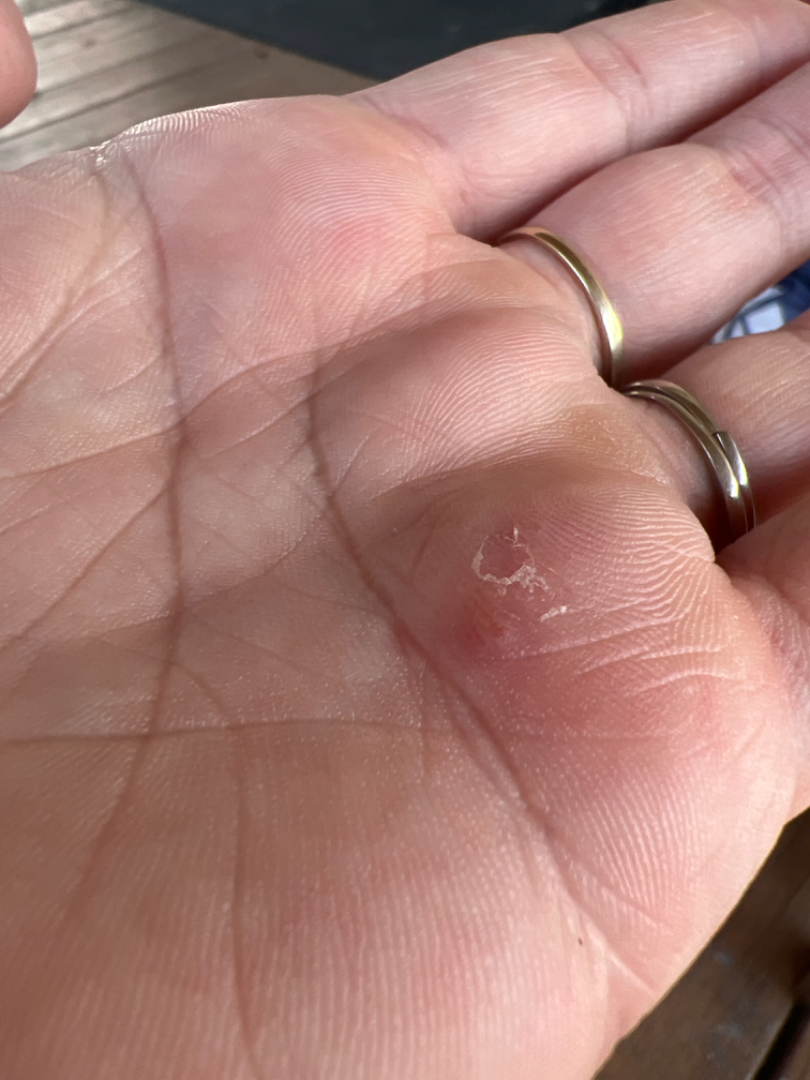image framing: at an angle | affected area: palm | subject: female, age 18–29 | differential: most likely Clavus; possibly Impetigo; also raised was Foreign body; also consider Herpes Simplex.